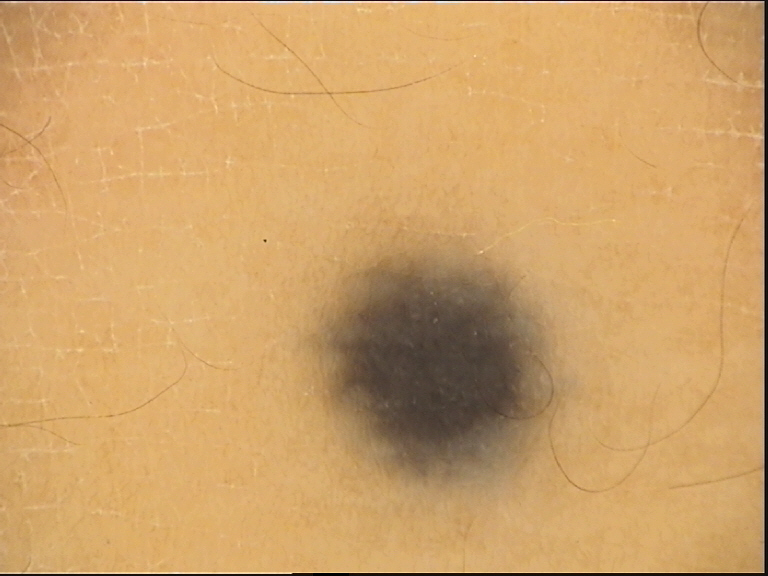The diagnostic label was a banal lesion — a blue nevus.